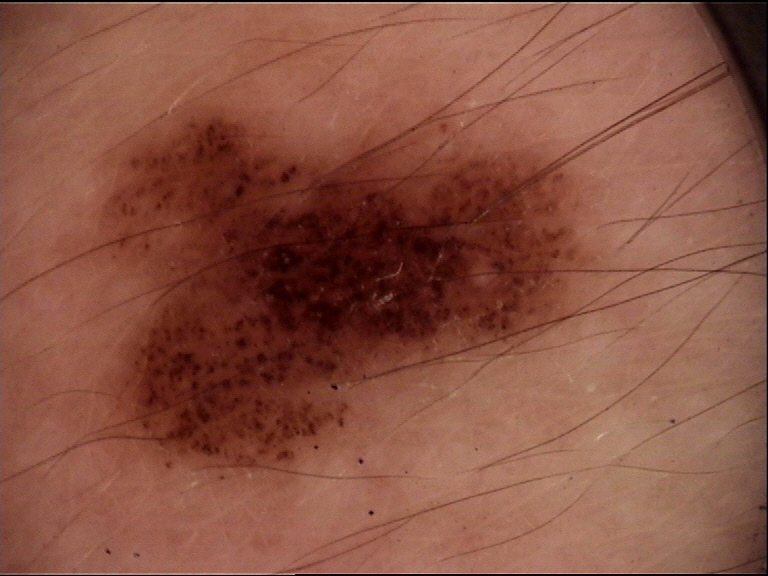{"diagnosis": {"name": "dysplastic compound nevus", "code": "cd", "malignancy": "benign", "super_class": "melanocytic", "confirmation": "expert consensus"}}